A skin lesion imaged with a dermatoscope: 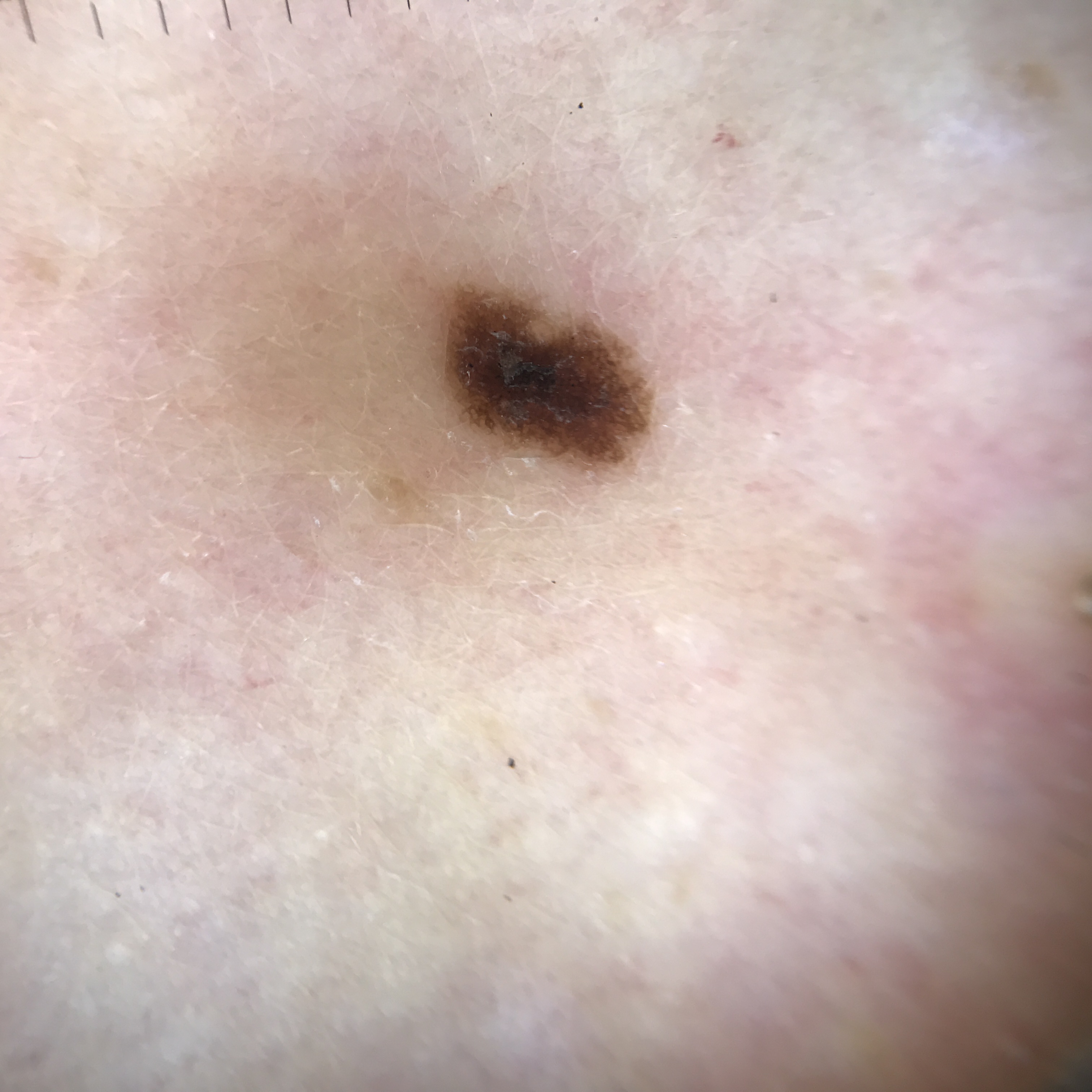Q: What was the diagnostic impression?
A: dysplastic junctional nevus (expert consensus)